A skin lesion imaged with a dermatoscope: 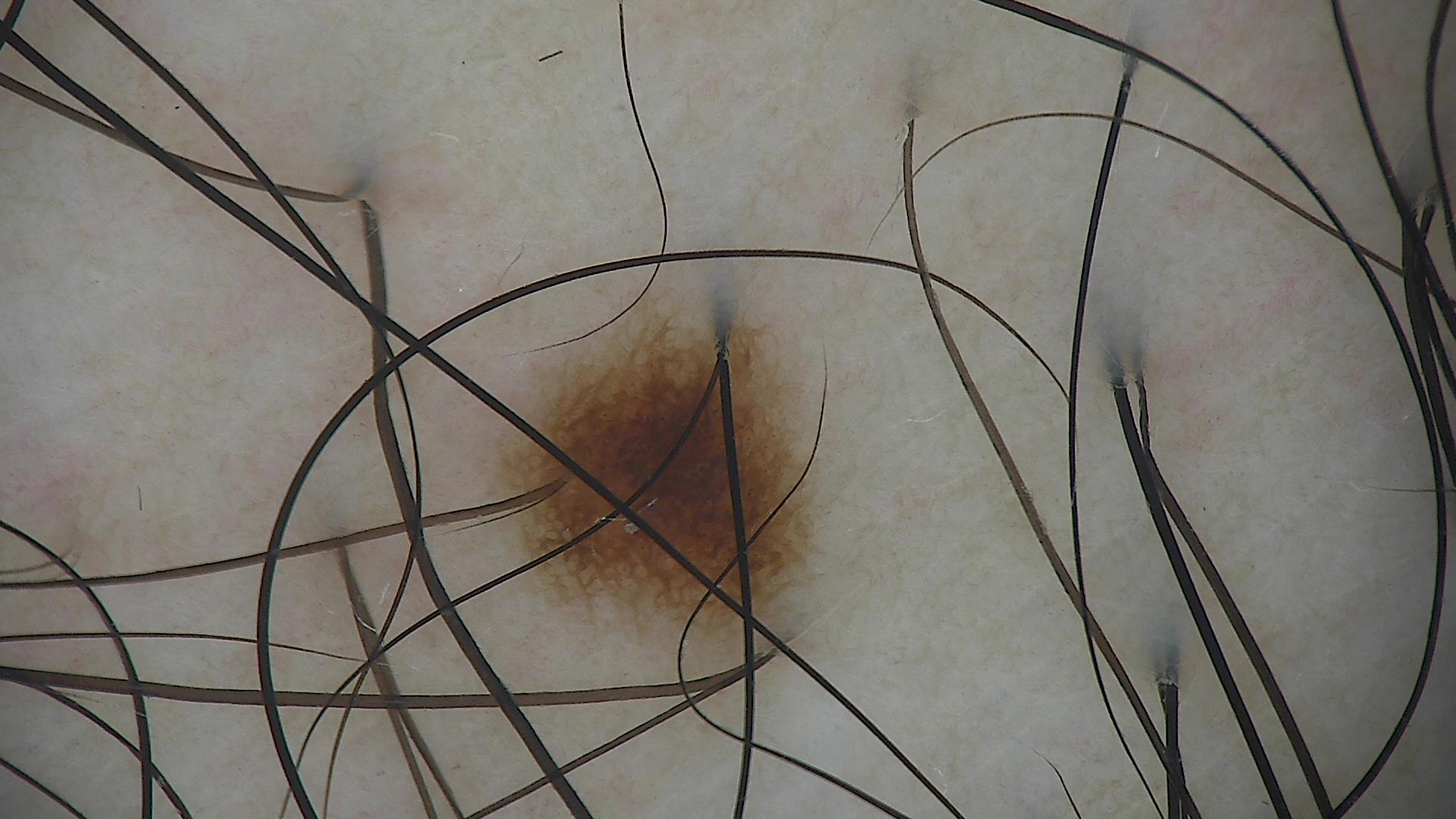Conclusion:
Diagnosed as a benign lesion — a dysplastic junctional nevus.